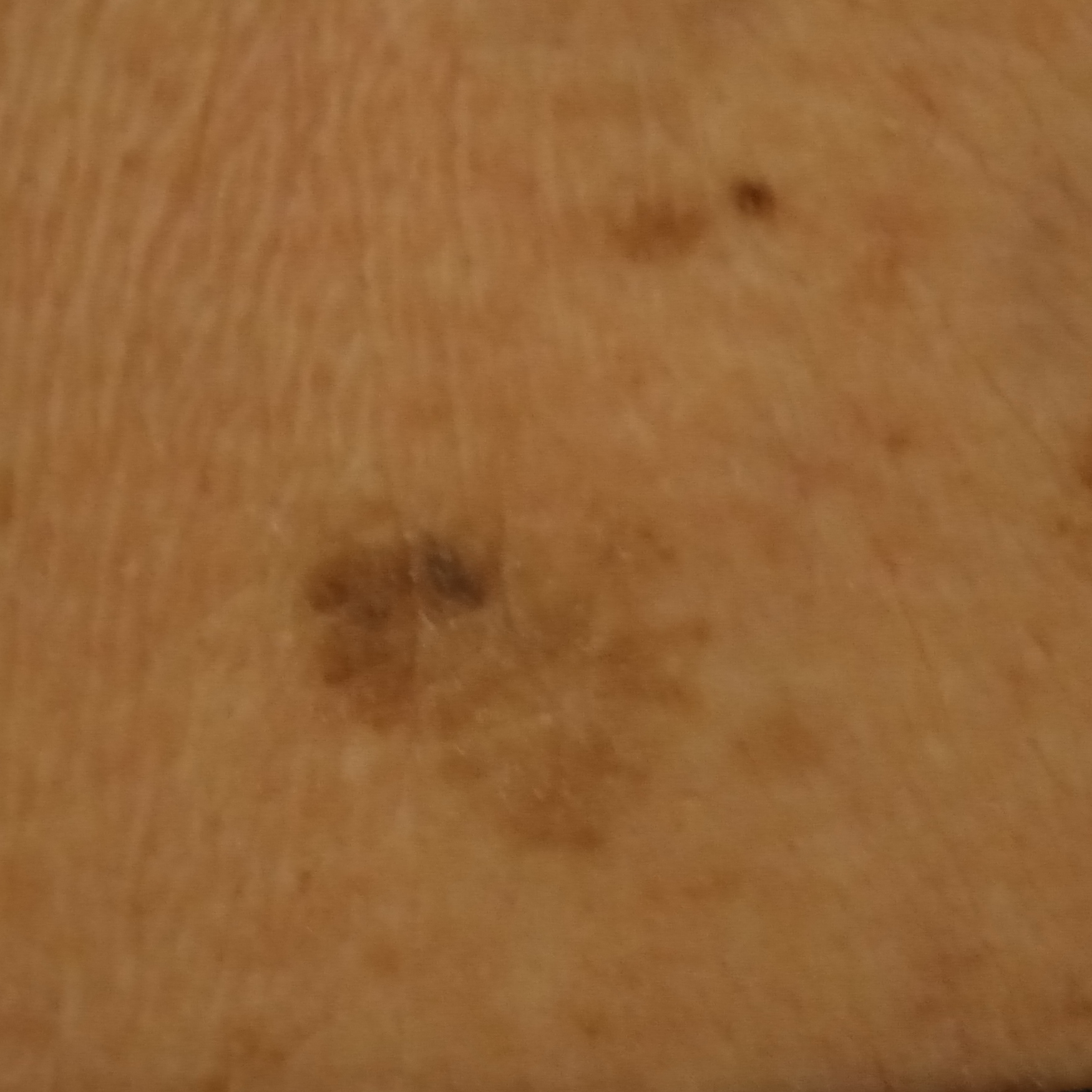The patient says their skin reddens painfully with sun exposure.
A macroscopic clinical photograph of a skin lesion.
A female patient aged 72.
The patient describes having a moderate number of moles.
Imaged for a research study, with no referral diagnosis recorded.
The lesion is located on the back.
The consensus diagnosis for this lesion was a seborrheic keratosis.